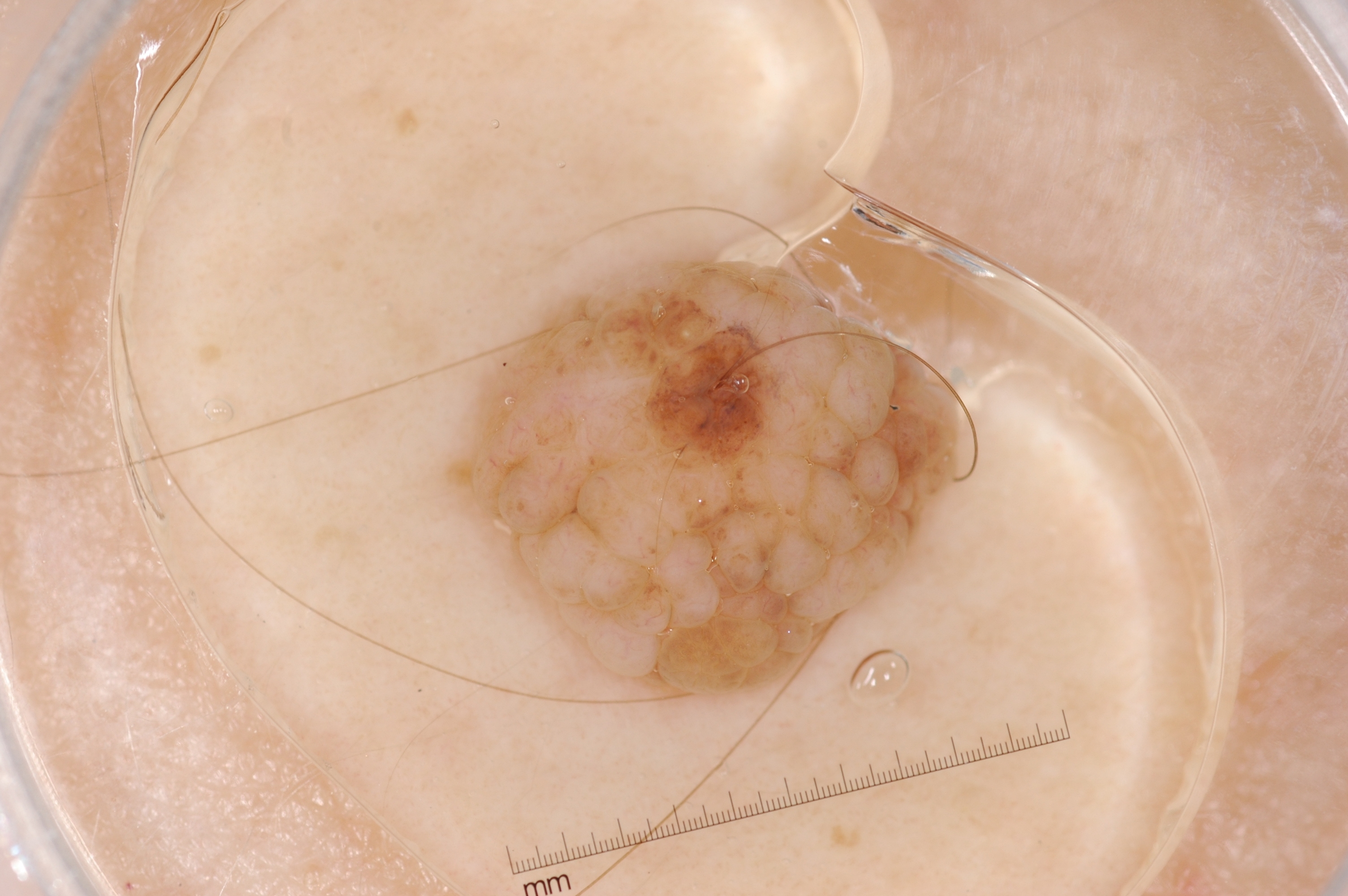Case summary:
• imaging · dermoscopic image
• bounding box · bbox(447, 258, 961, 698)
• features · milia-like cysts
• diagnostic label · a melanocytic nevus